A female patient approximately 80 years of age; Fitzpatrick skin type II; a clinical photograph of a skin lesion — 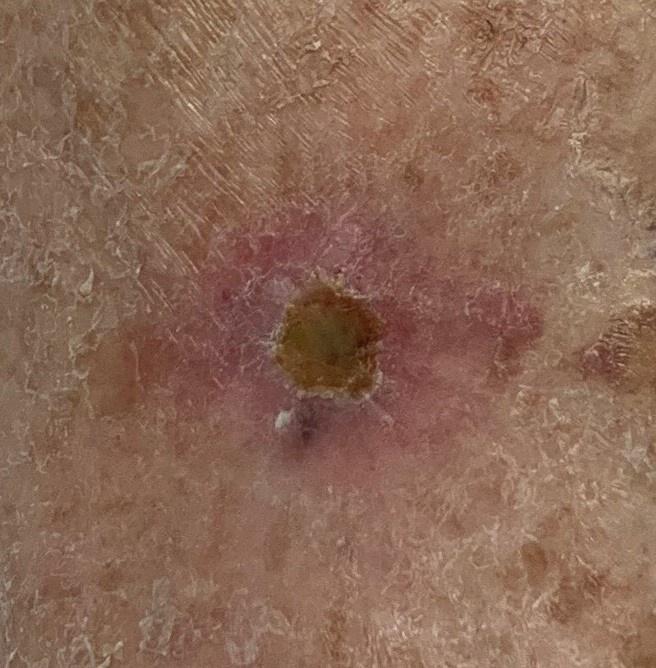diagnostic label — Squamous cell carcinoma (biopsy-proven).